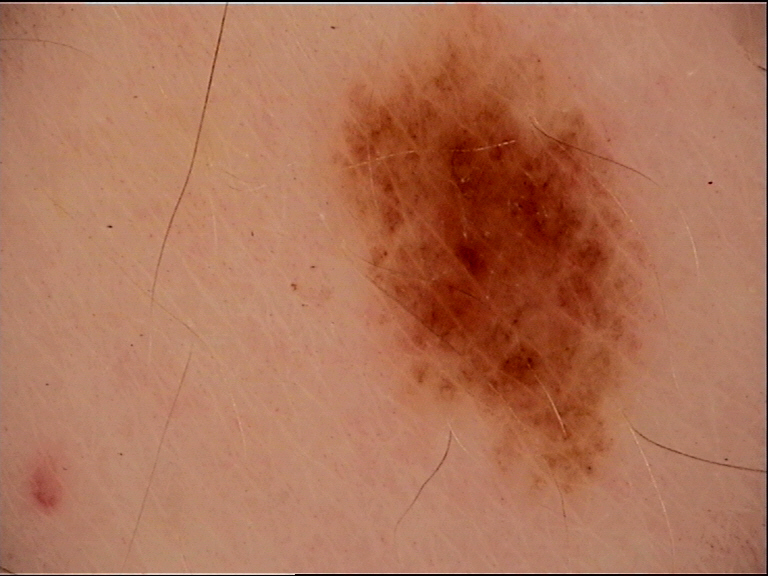image: dermatoscopy
diagnosis:
  name: dysplastic junctional nevus
  code: jd
  malignancy: benign
  super_class: melanocytic
  confirmation: expert consensus